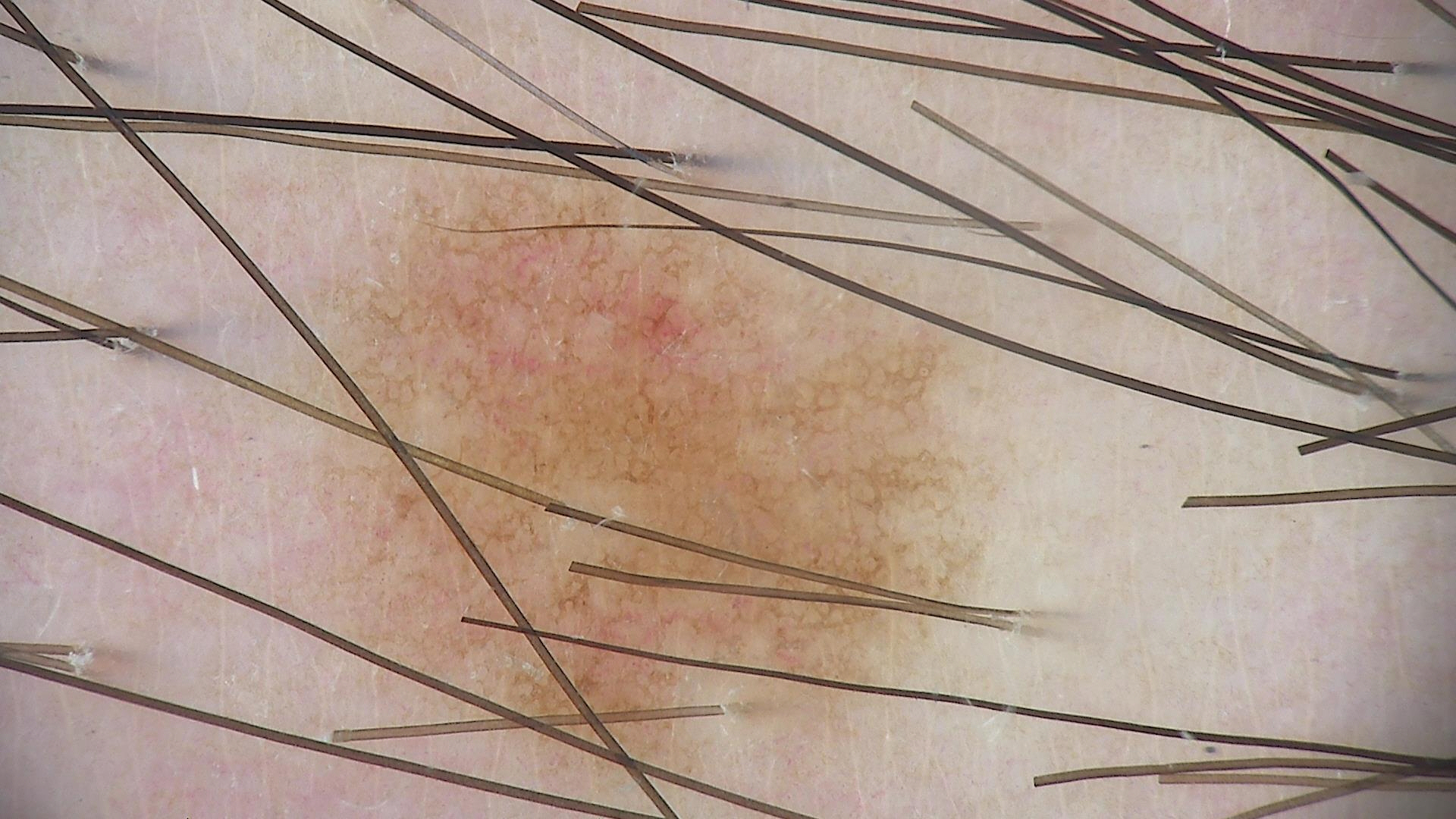Findings: A dermoscopy image of a single skin lesion. Impression: Diagnosed as a benign lesion — a dysplastic junctional nevus.